Present for about one day; this image was taken at an angle; the patient is 18–29, female; texture is reported as raised or bumpy; located on the palm, top or side of the foot, sole of the foot, leg, back of the hand and arm:
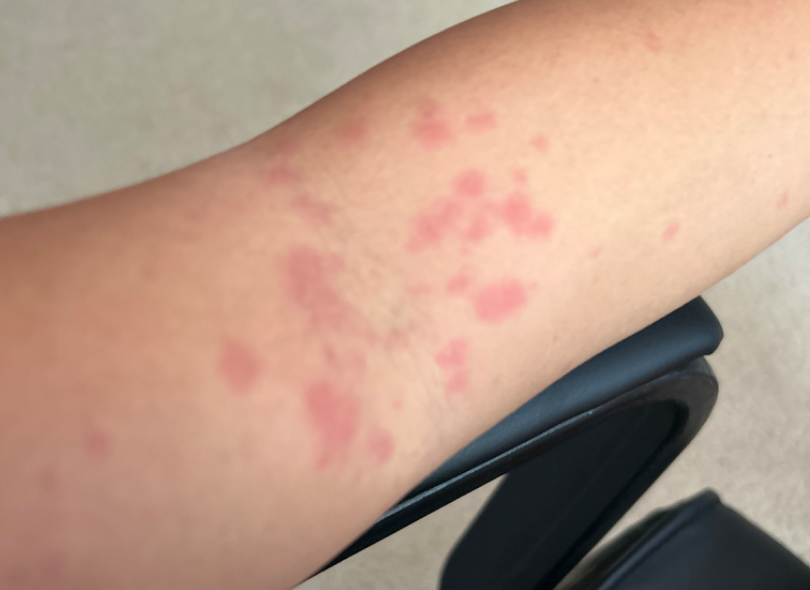{
  "differential": {
    "leading": [
      "Urticaria"
    ],
    "considered": [
      "Erythema multiforme",
      "Allergic Contact Dermatitis"
    ]
  }
}